A clinical photo of a skin lesion taken with a smartphone. History notes prior skin cancer (patient or family) and prior malignancy (patient or family):
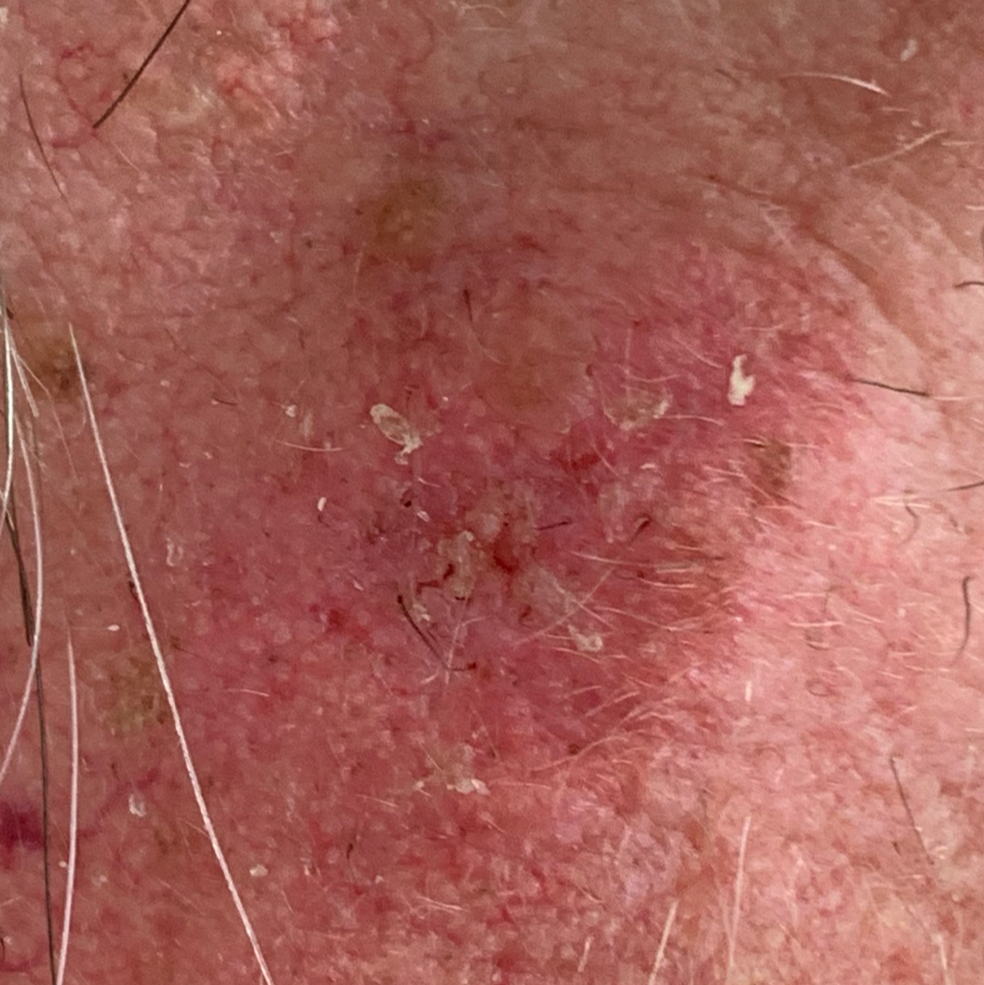Q: What is the anatomic site?
A: a forearm
Q: How large is the lesion?
A: 12x10 mm
Q: What does the patient describe?
A: itching / no bleeding, no pain
Q: What is this lesion?
A: basal cell carcinoma (biopsy-proven)